A female patient 15 years of age · imaged for a research study, with no referral diagnosis recorded · few moles overall by the patient's own estimate · the patient says their skin reddens with sun exposure.
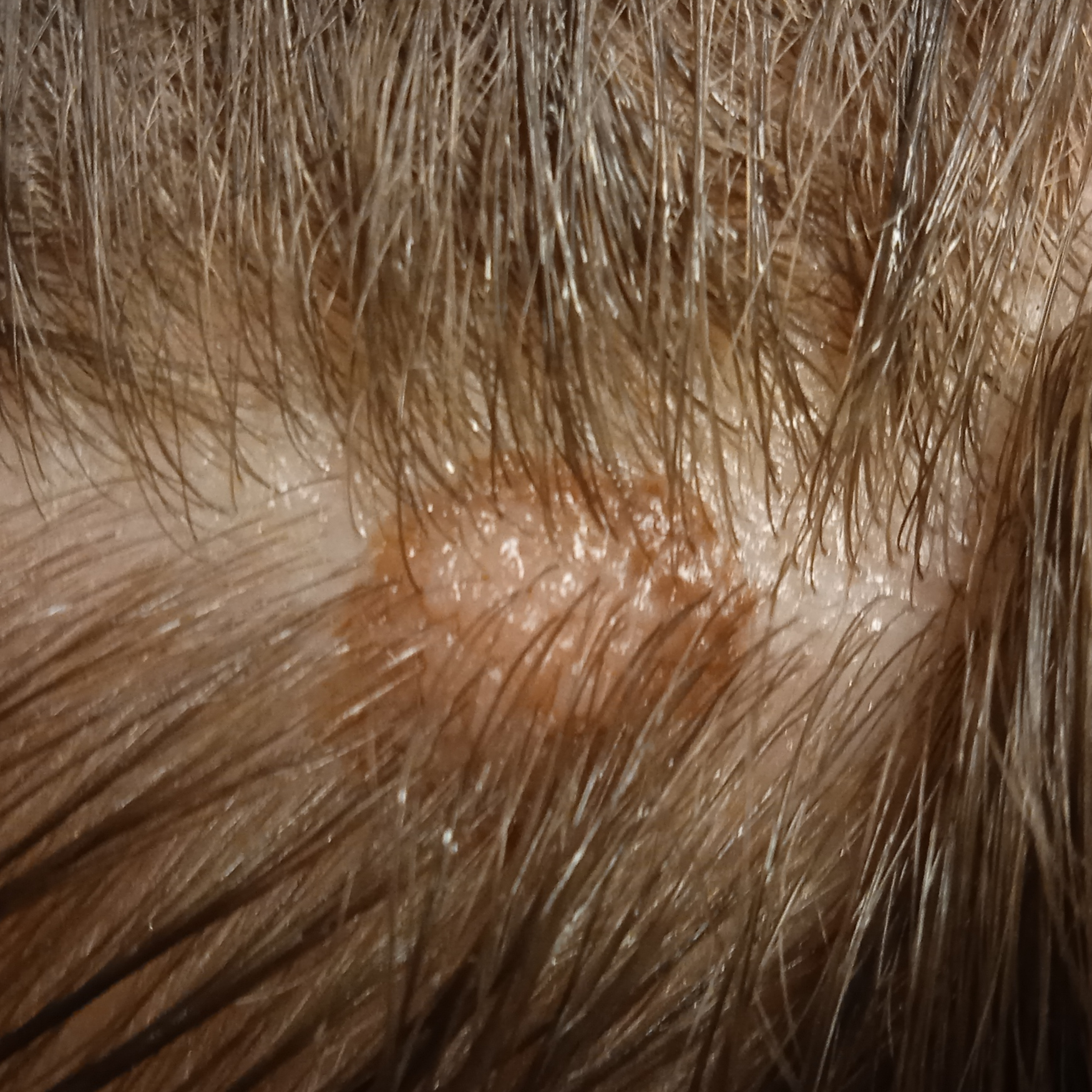{"lesion_size": {"diameter_mm": 9.1}, "diagnosis": {"name": "melanocytic nevus", "malignancy": "benign"}}